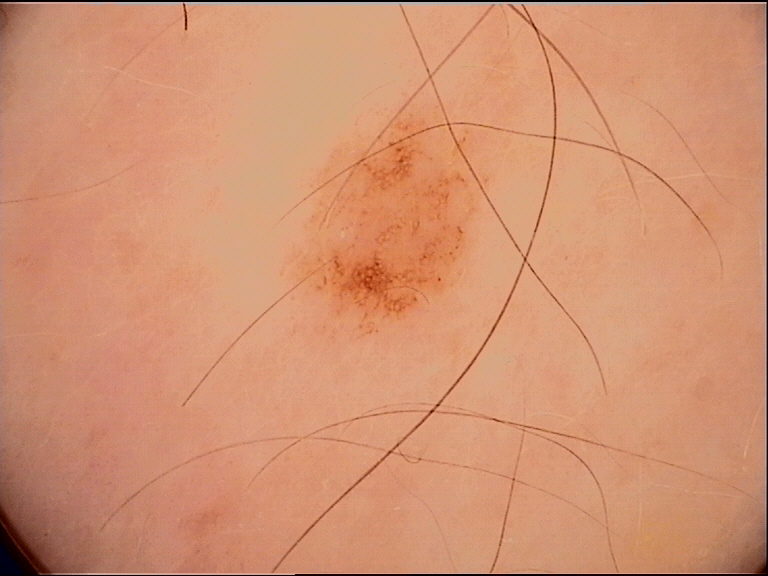A dermatoscopic image of a skin lesion. Classified as a dysplastic junctional nevus.